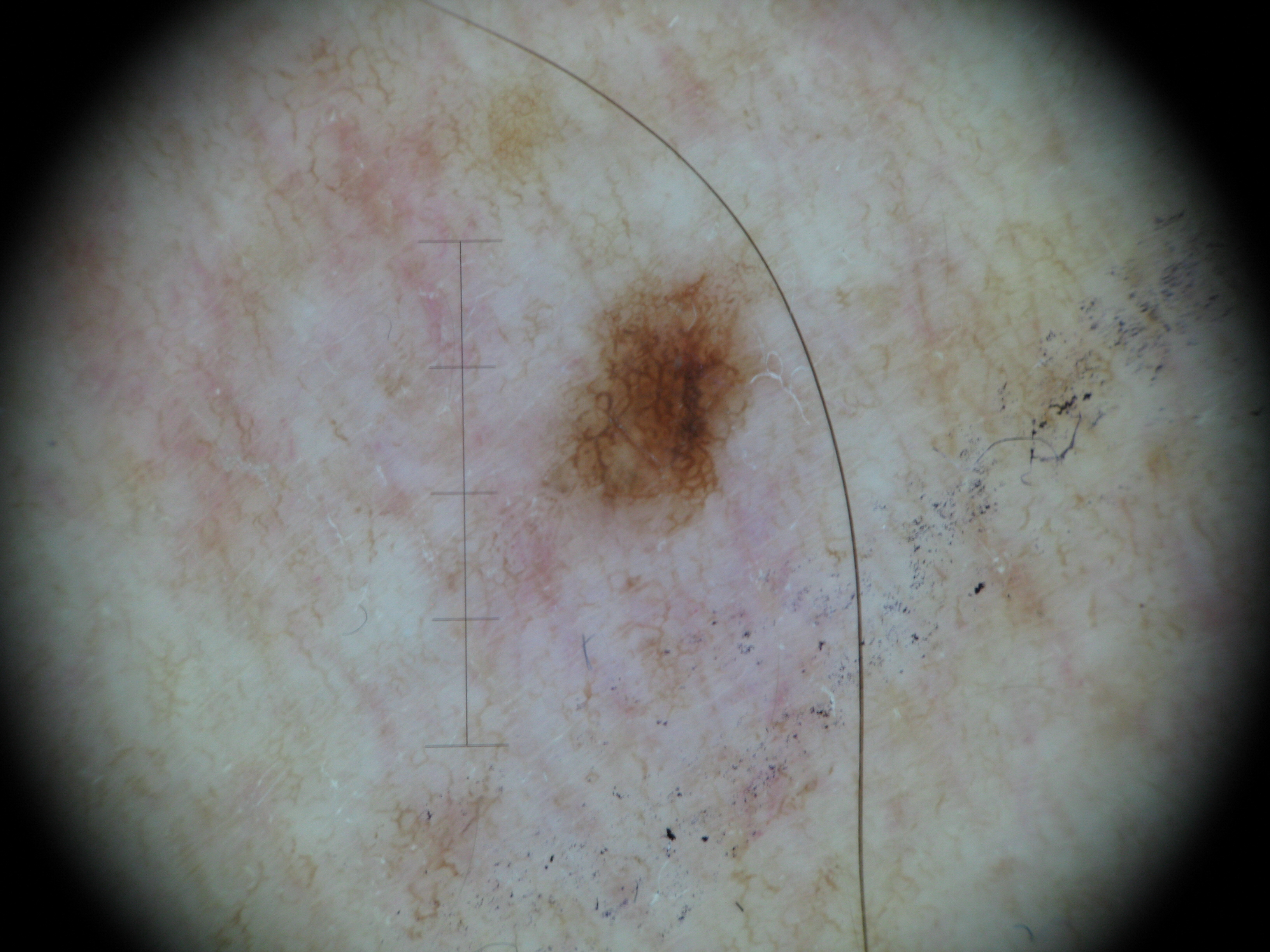The diagnosis was a dysplastic junctional nevus.